Female subject, age 18–29; located on the front of the torso, arm, back of the torso and leg; a close-up photograph:
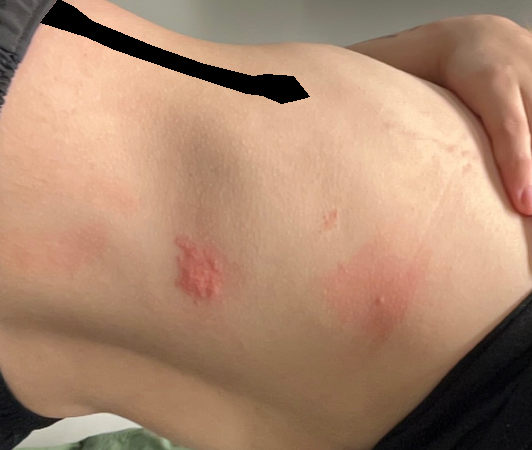assessment — three dermatologists each reviewed the case: the leading impression is Allergic Contact Dermatitis; an alternative is Sweet syndrome